A clinical photo of a skin lesion taken with a smartphone; a patient 67 years of age — 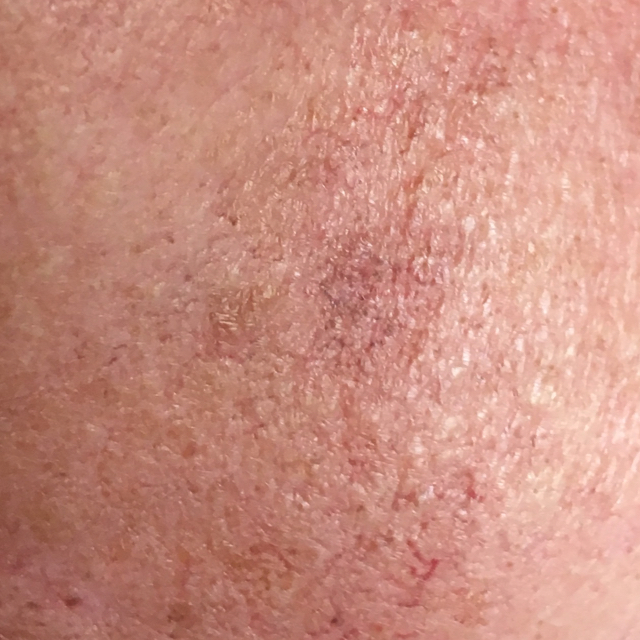Located on the face.
The patient describes that the lesion has not bled and has not grown.
Diagnosed by dermatologist consensus as an actinic keratosis.